A dermoscopy image of a single skin lesion.
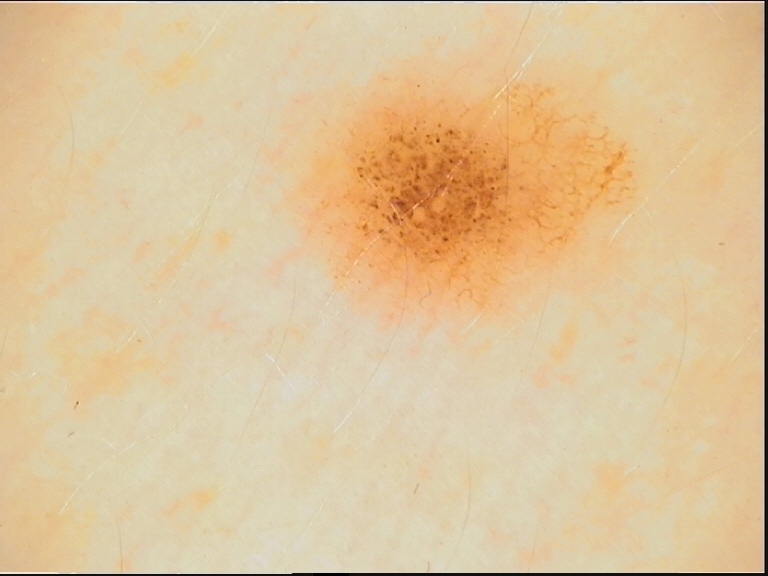diagnostic label = acral dysplastic junctional nevus (expert consensus).